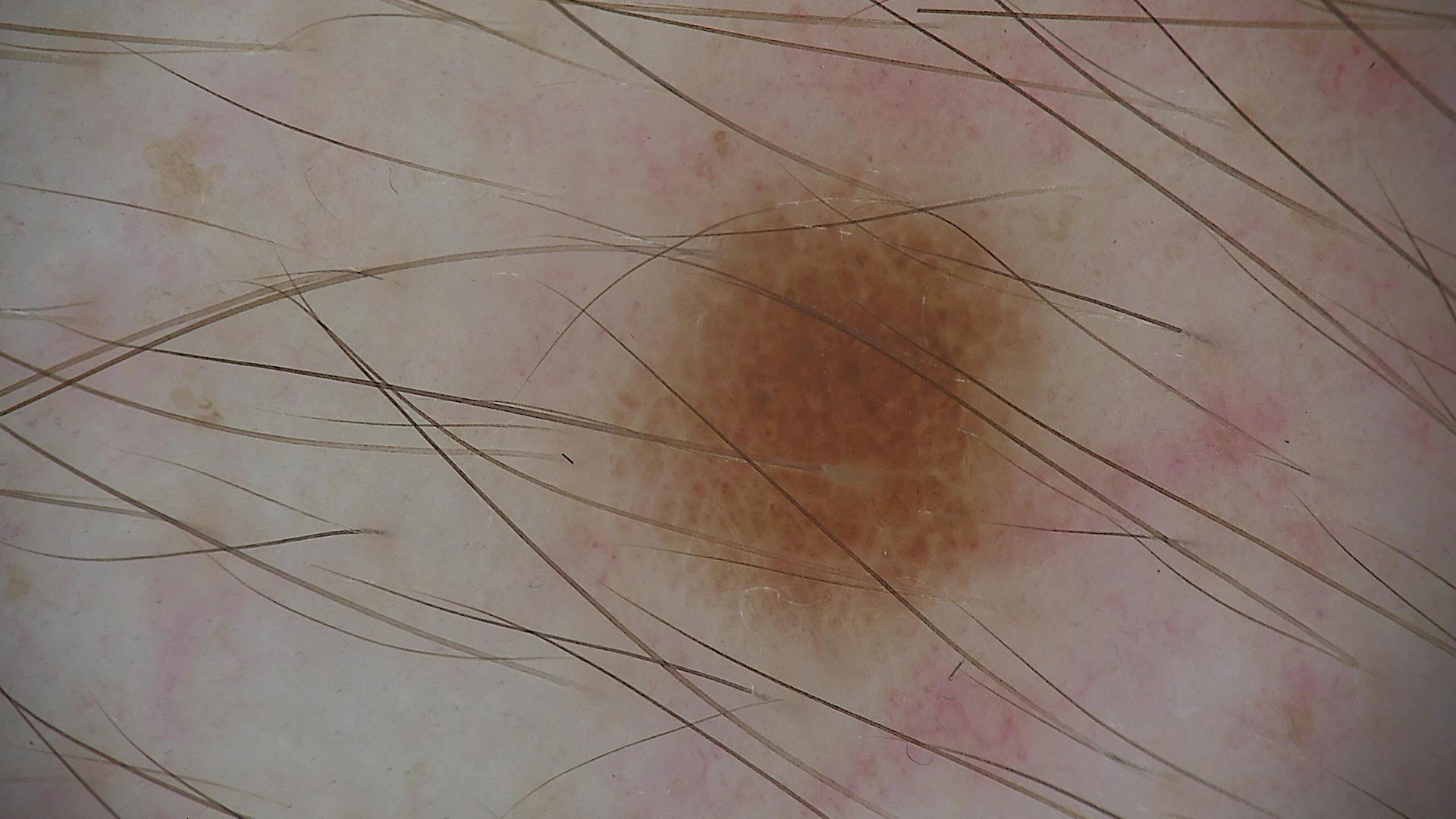Findings:
- imaging: dermatoscopy
- assessment: dysplastic junctional nevus (expert consensus)